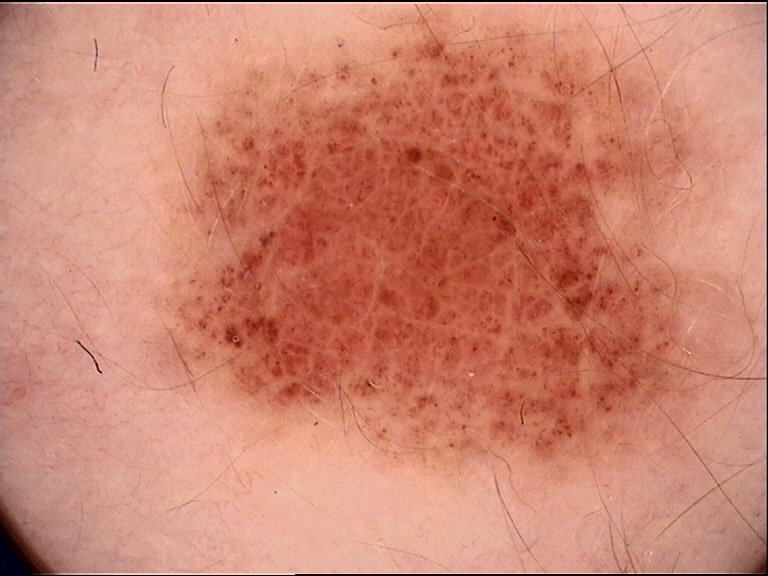A skin lesion imaged with a dermatoscope. The diagnosis was a banal lesion — a compound nevus.